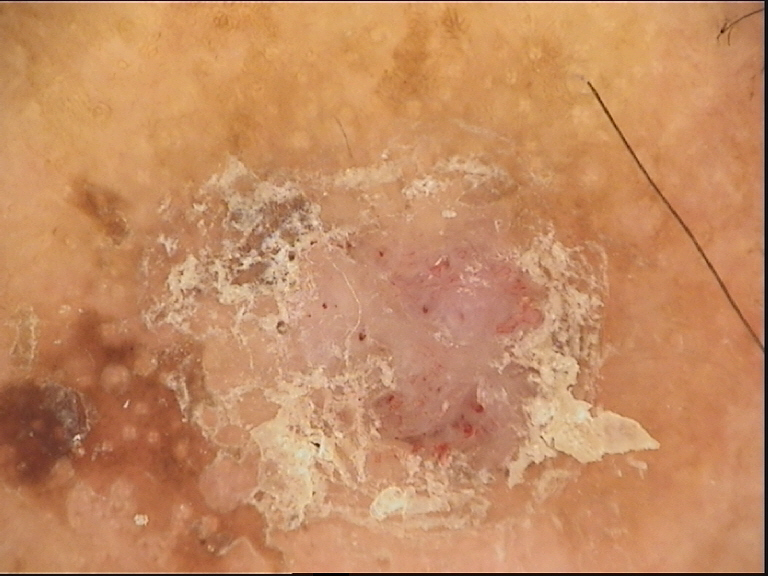A skin lesion imaged with a dermatoscope. The morphology is that of a keratinocytic lesion. Labeled as a seborrheic keratosis.